The subject is 30–39, female; close-up view.
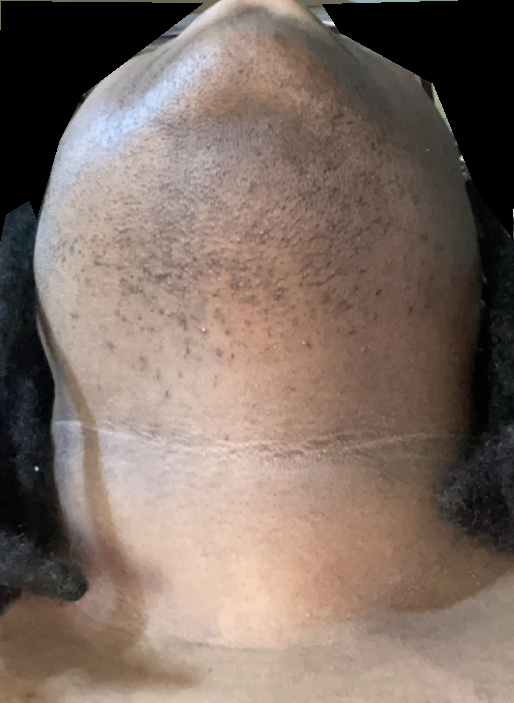The reviewing clinician's impression was: the leading consideration is Post-Inflammatory hyperpigmentation; possibly Folliculitis; the differential also includes Scar Condition.